A dermoscopic image of a skin lesion: 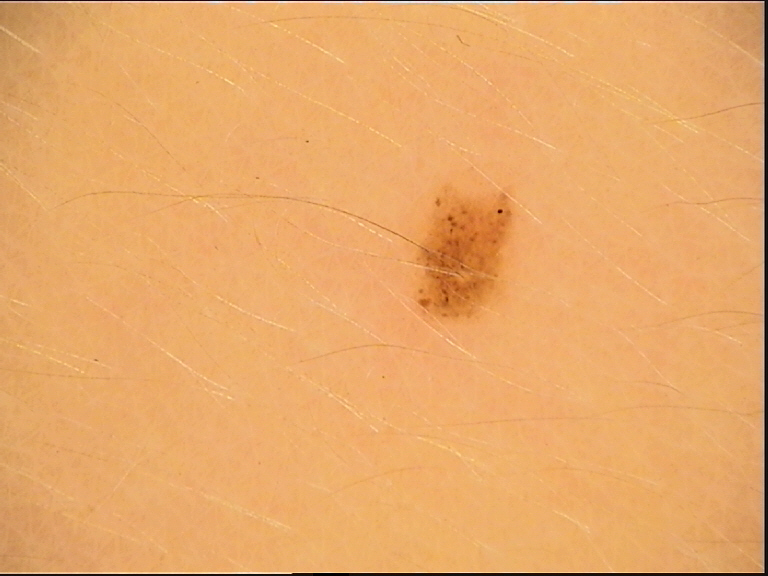Consistent with a banal lesion — a junctional nevus.